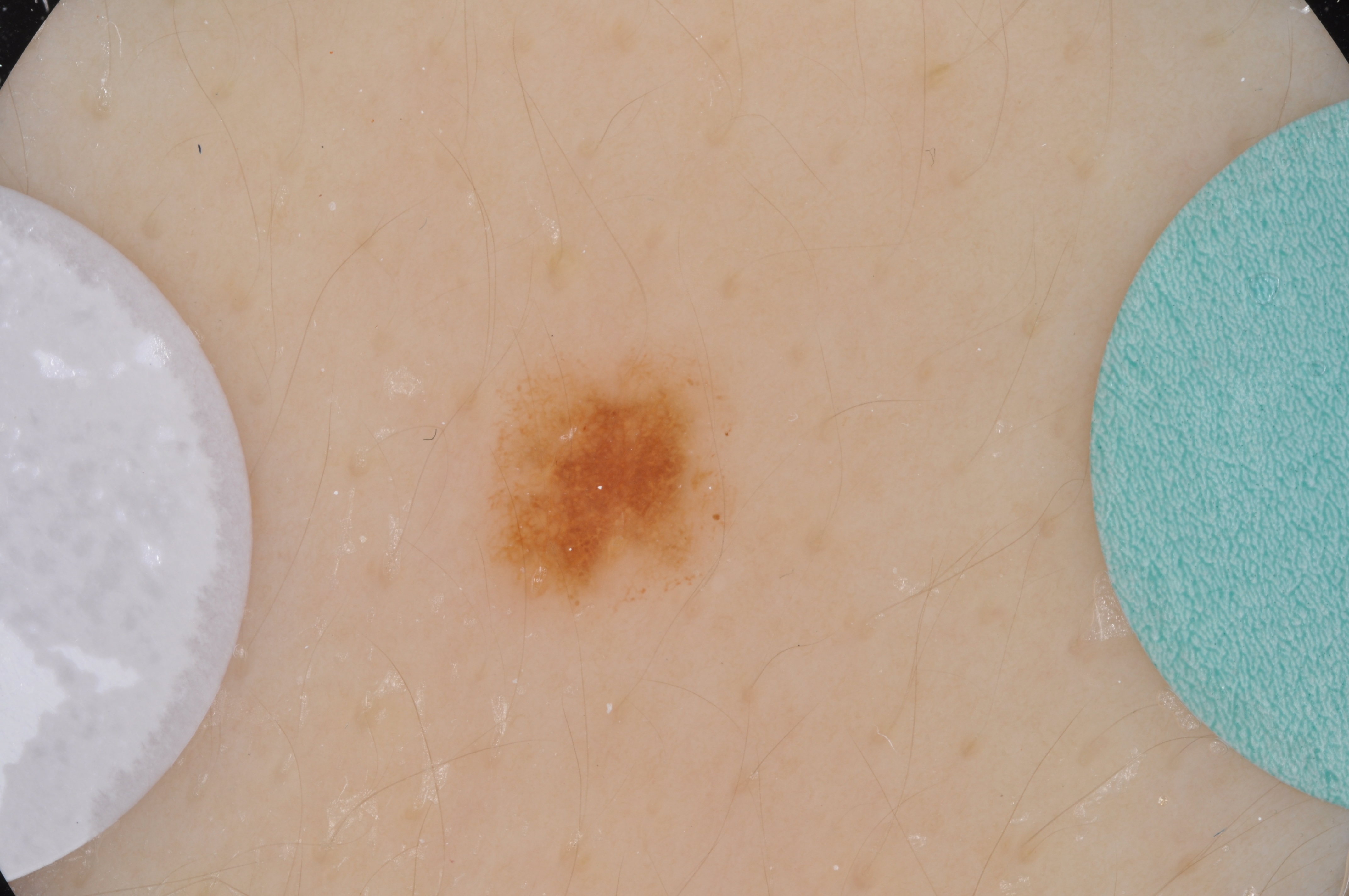| field | value |
|---|---|
| image type | dermoscopy of a skin lesion |
| patient | female, aged approximately 15 |
| lesion location | bbox=[485, 342, 750, 619] |
| features | negative network and pigment network |
| impression | a melanocytic nevus, a benign lesion |